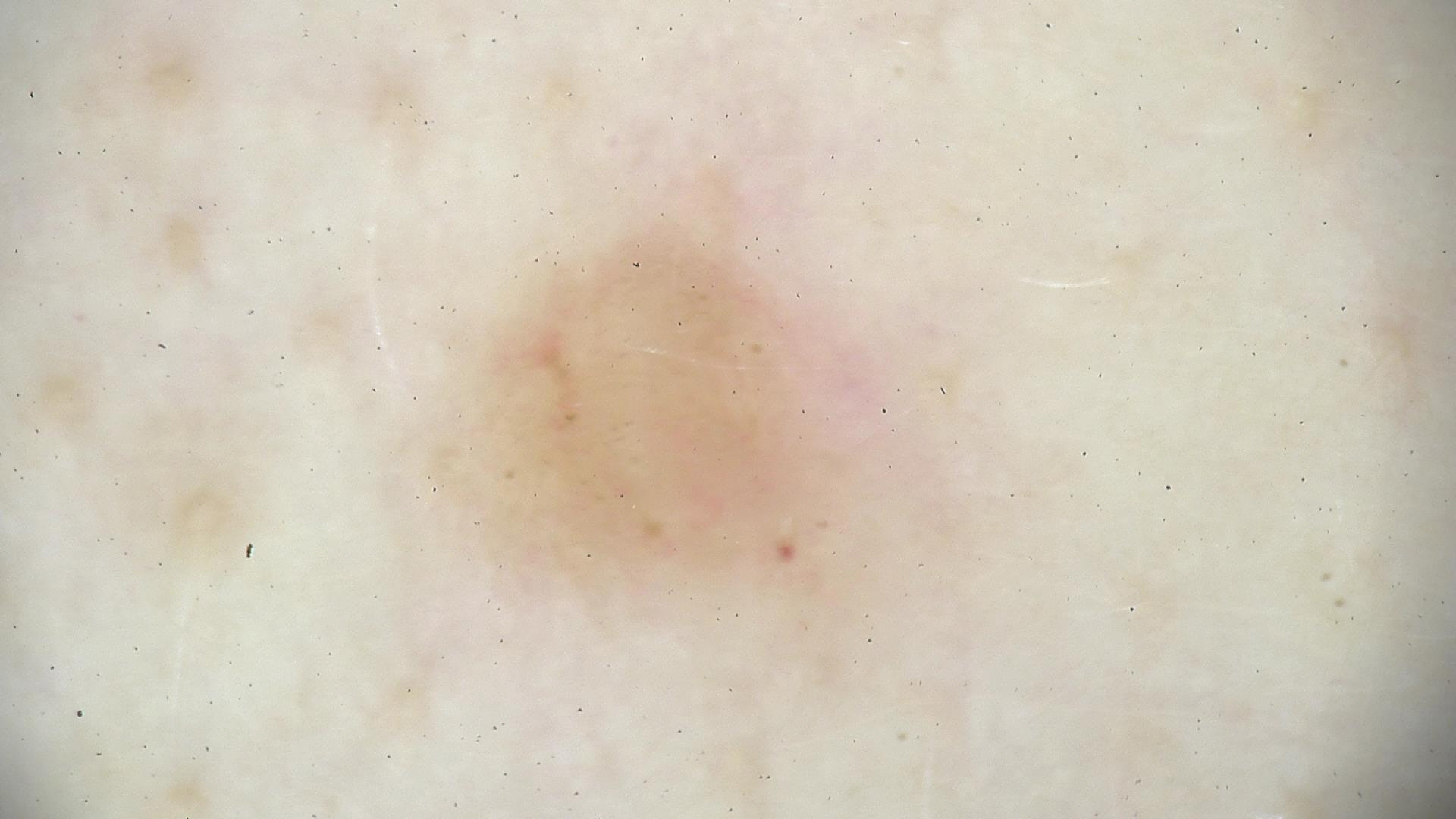diagnostic label: dermal nevus (expert consensus).